The patient describes having numerous moles. A clinical close-up of a skin lesion. Collected as part of a research study, without a referral diagnosis. By self-report, a family history of skin cancer, a personal history of cancer, and a personal history of skin cancer. The patient says their skin tans without first burning: 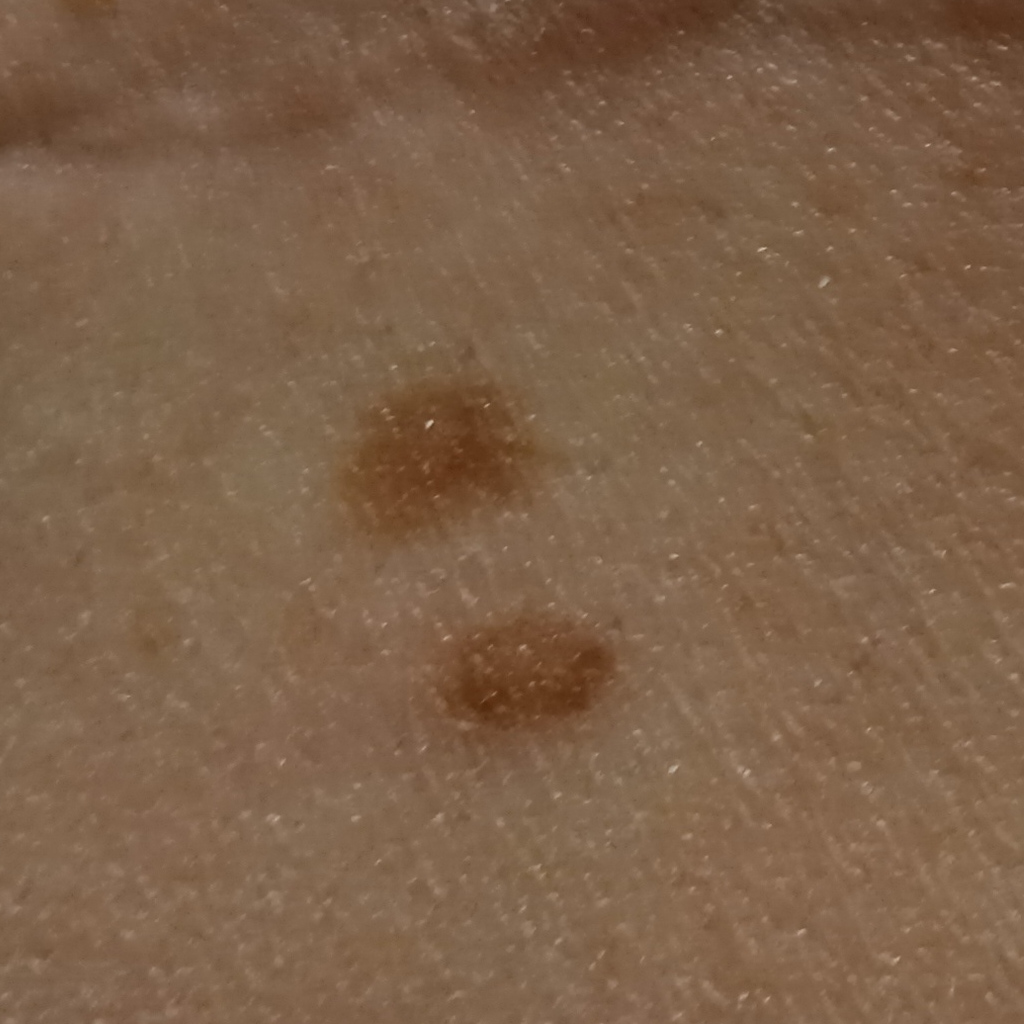<case>
  <lesion_location>the back</lesion_location>
  <lesion_size>
    <diameter_mm>8.6</diameter_mm>
  </lesion_size>
  <diagnosis>
    <name>atypical (dysplastic) nevus</name>
    <malignancy>benign</malignancy>
  </diagnosis>
</case>